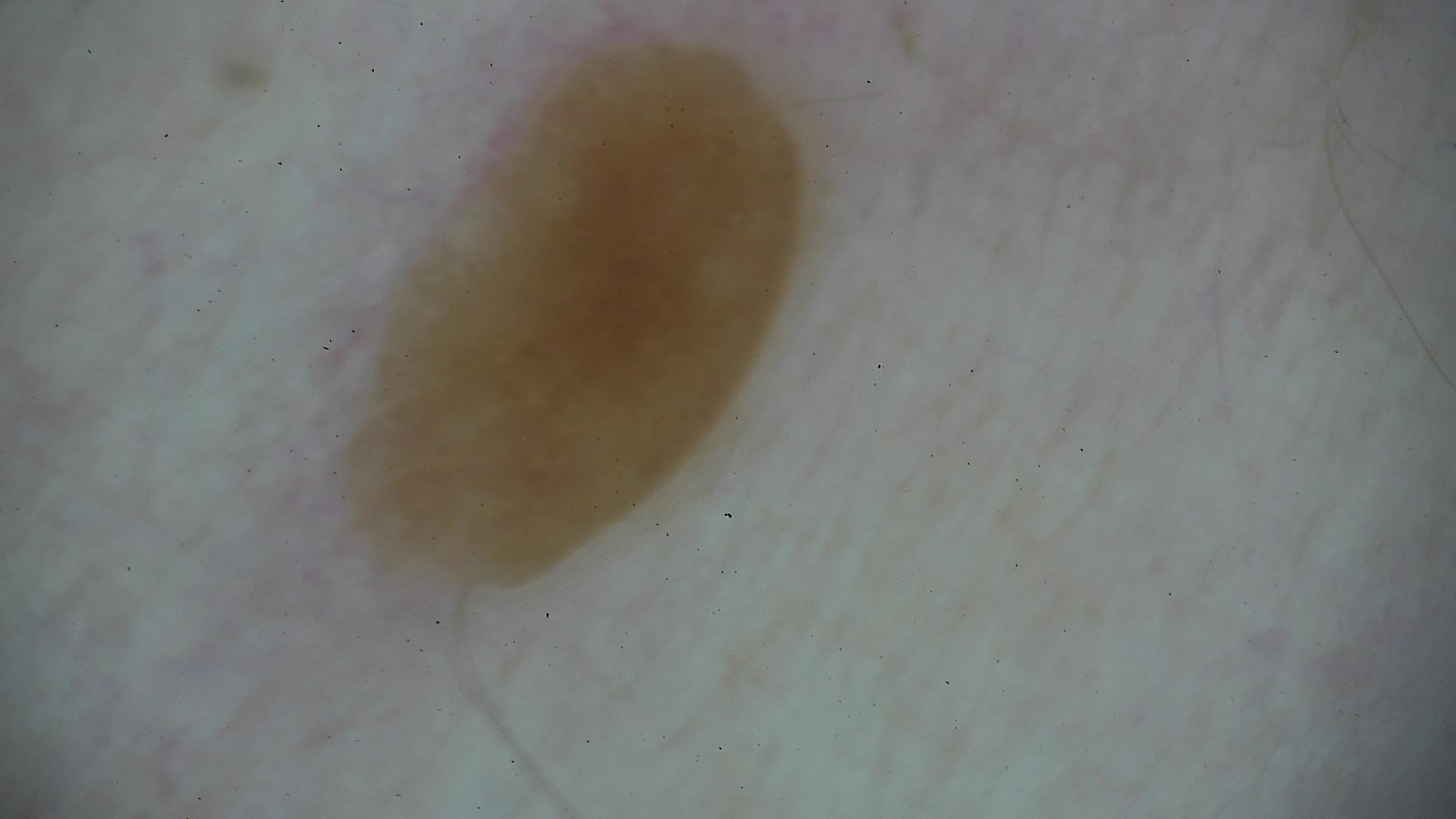Dermoscopy of a skin lesion.
The architecture is that of a keratinocytic lesion.
The diagnostic label was a seborrheic keratosis.